The chart notes prior malignancy (patient or family); a female subject in their 70s; the patient is Fitzpatrick II; a smartphone photograph of a skin lesion — 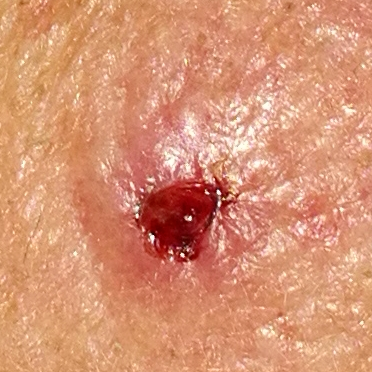anatomic site = the face
lesion size = 10x7 mm
patient-reported symptoms = elevation, itching, pain, bleeding
diagnosis = basal cell carcinoma (biopsy-proven)